A dermoscopy image of a single skin lesion.
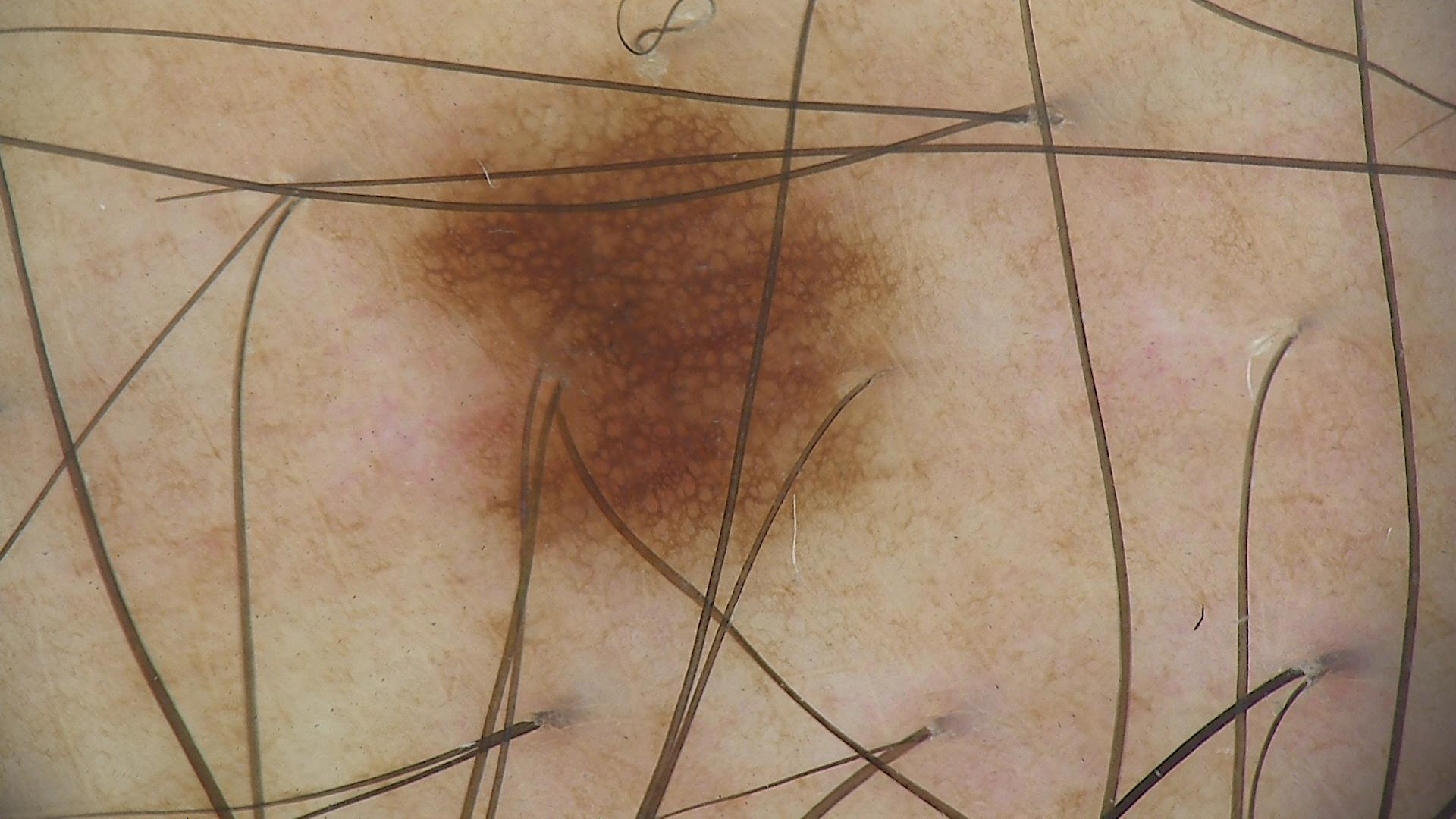Consistent with a benign lesion — a dysplastic junctional nevus.